A dermatoscopic image of a skin lesion:
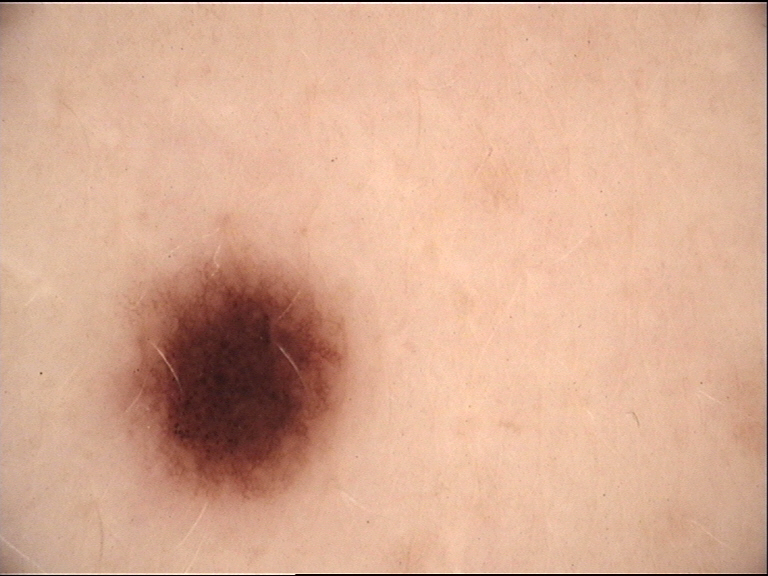subtype = banal; label = junctional nevus (expert consensus).